Close-up view; the patient indicates burning; the patient indicates the lesion is raised or bumpy; self-categorized by the patient as a rash; the affected area is the leg; skin tone: Fitzpatrick III: 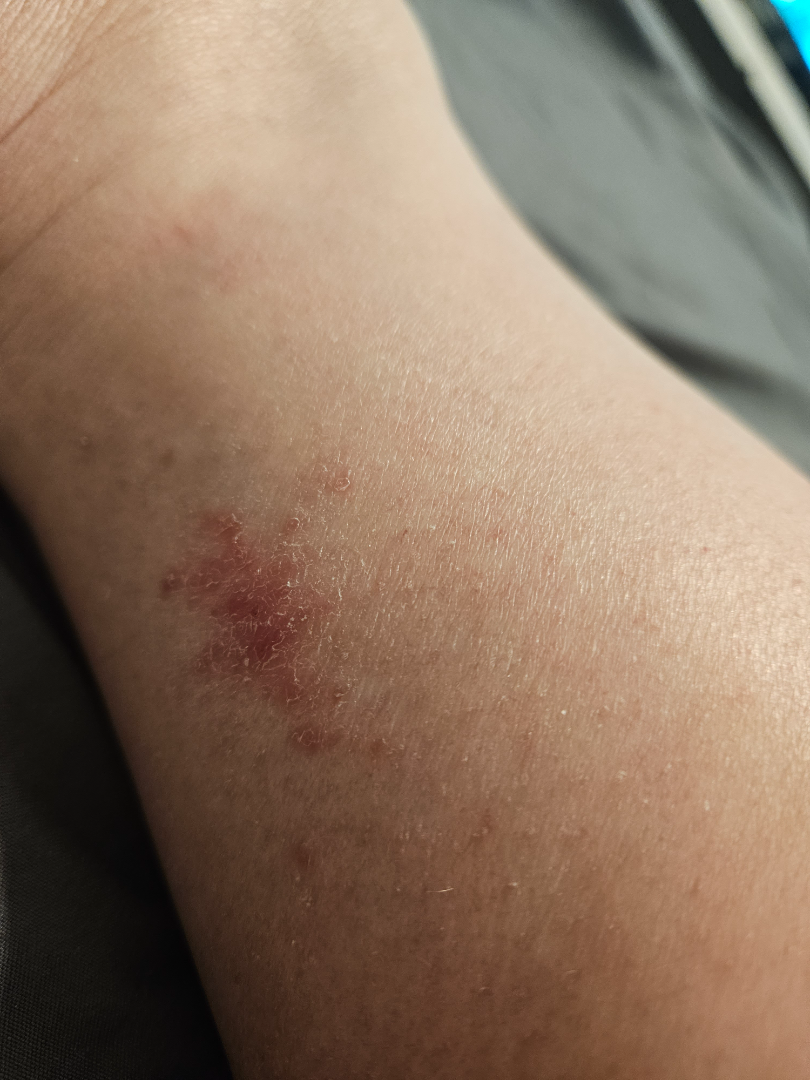On photographic review by a dermatologist, favoring Eczema; an alternative is Psoriasis.